A dermoscopic close-up of a skin lesion: 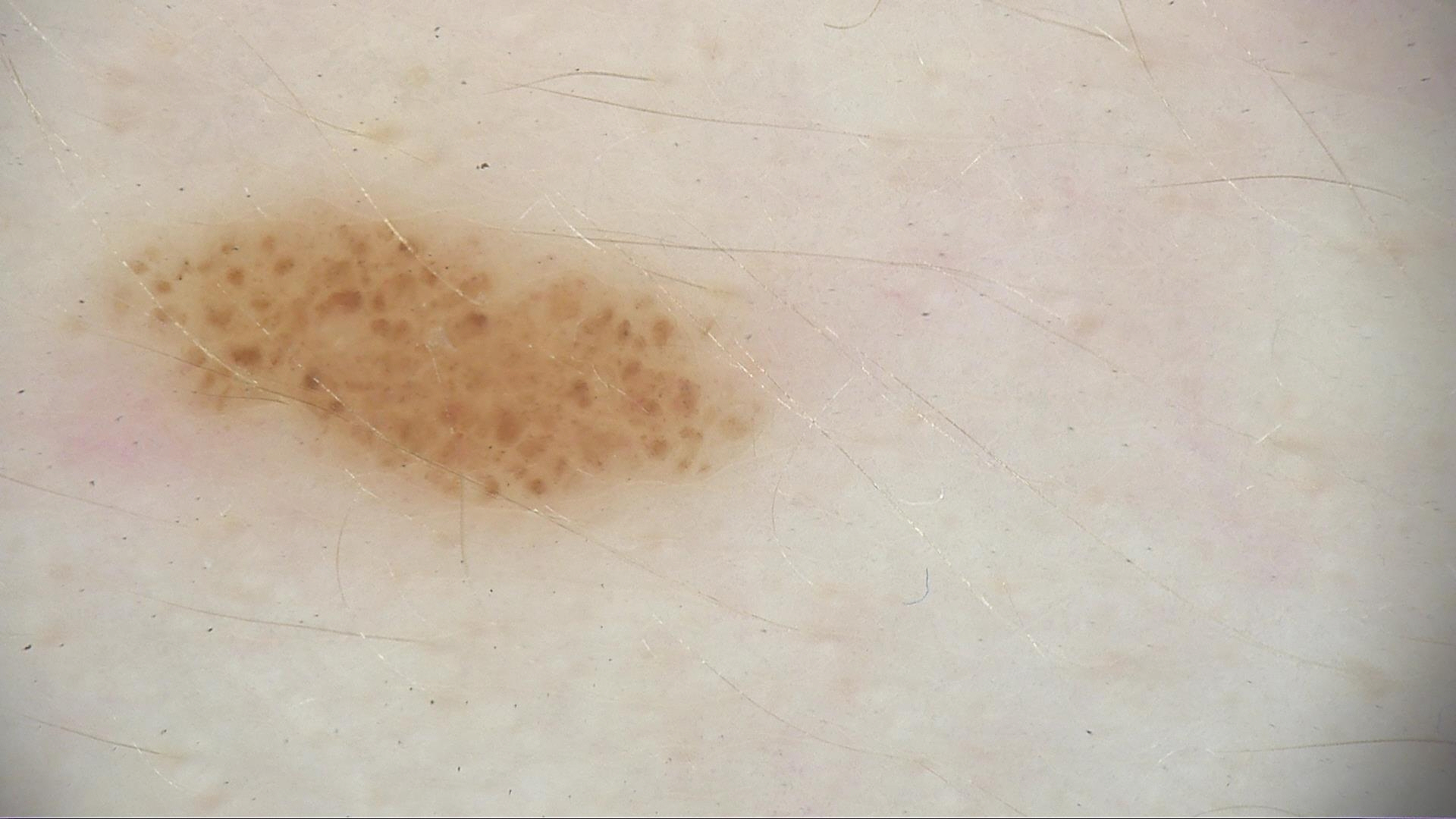Consistent with a banal lesion — a junctional nevus.